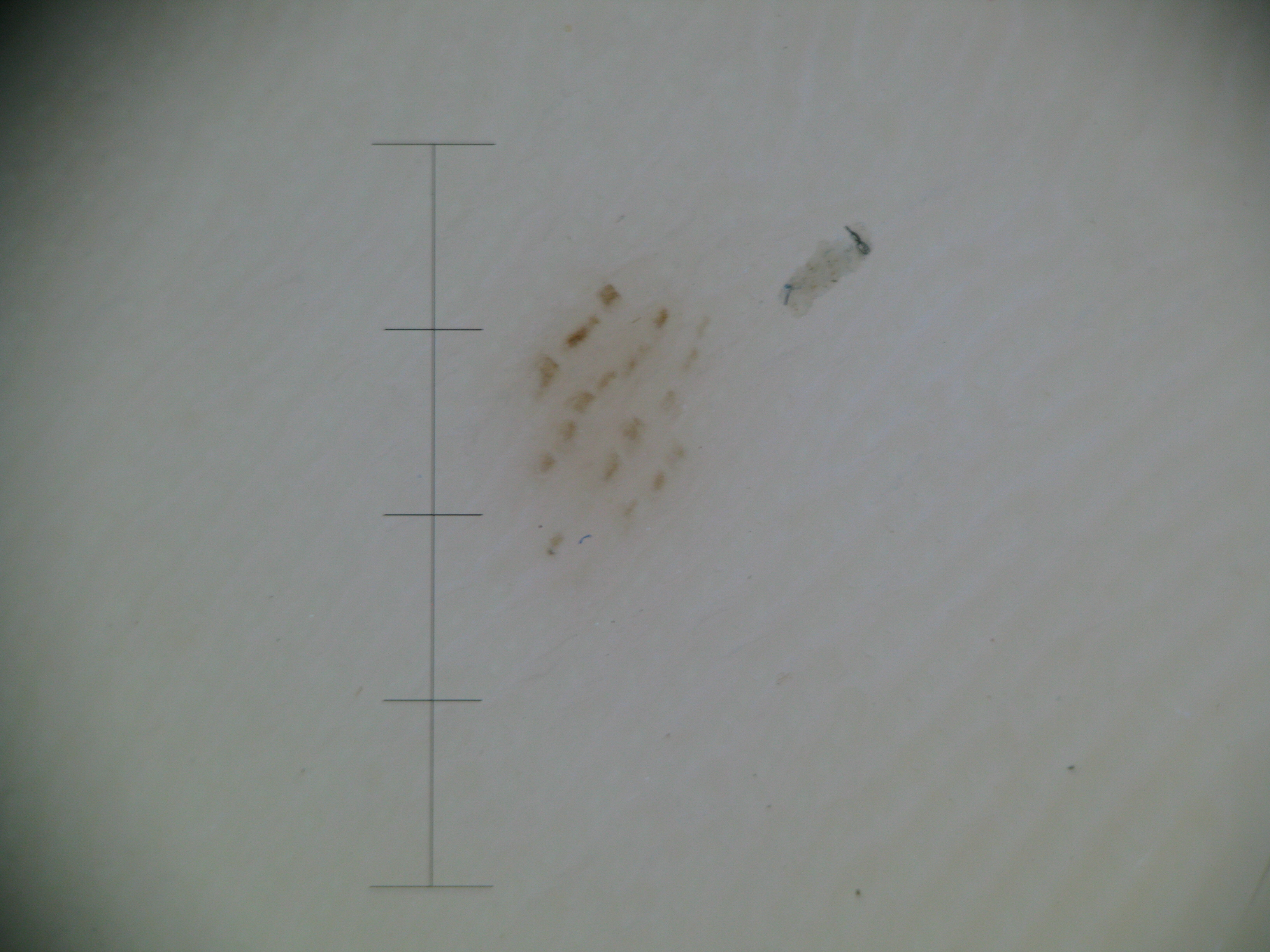Case: Dermoscopy of a skin lesion. The morphology is that of a banal lesion. Impression: Consistent with an acral junctional nevus.